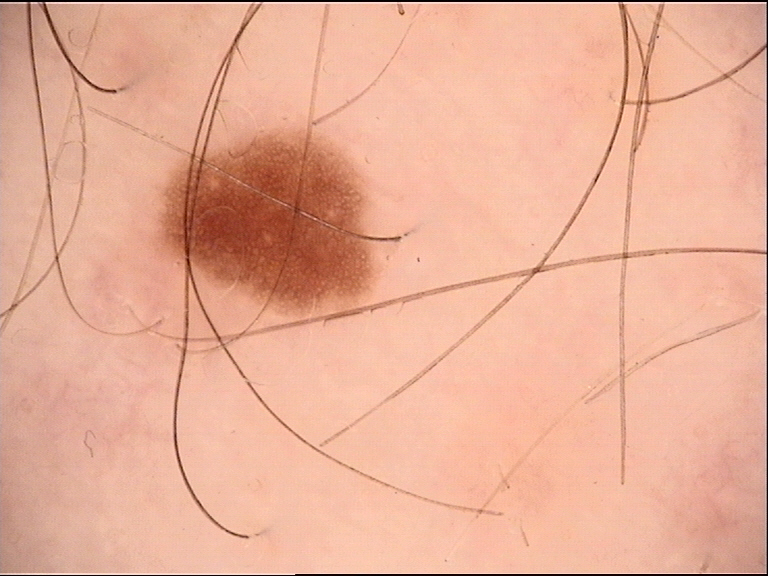Consistent with a dysplastic junctional nevus.